A skin lesion imaged with a dermatoscope.
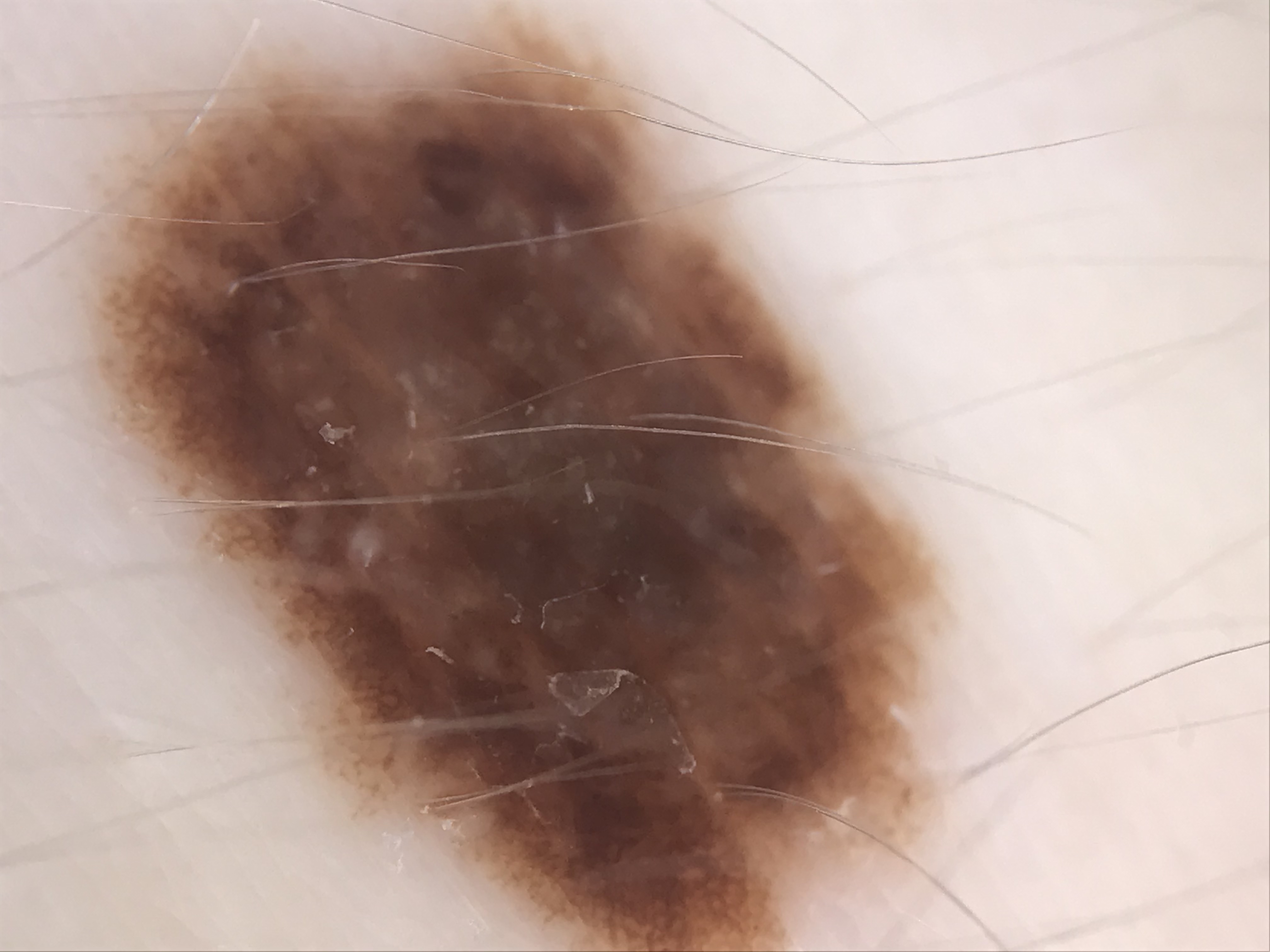diagnostic label=dysplastic compound nevus (expert consensus).